Dermoscopy of a skin lesion:
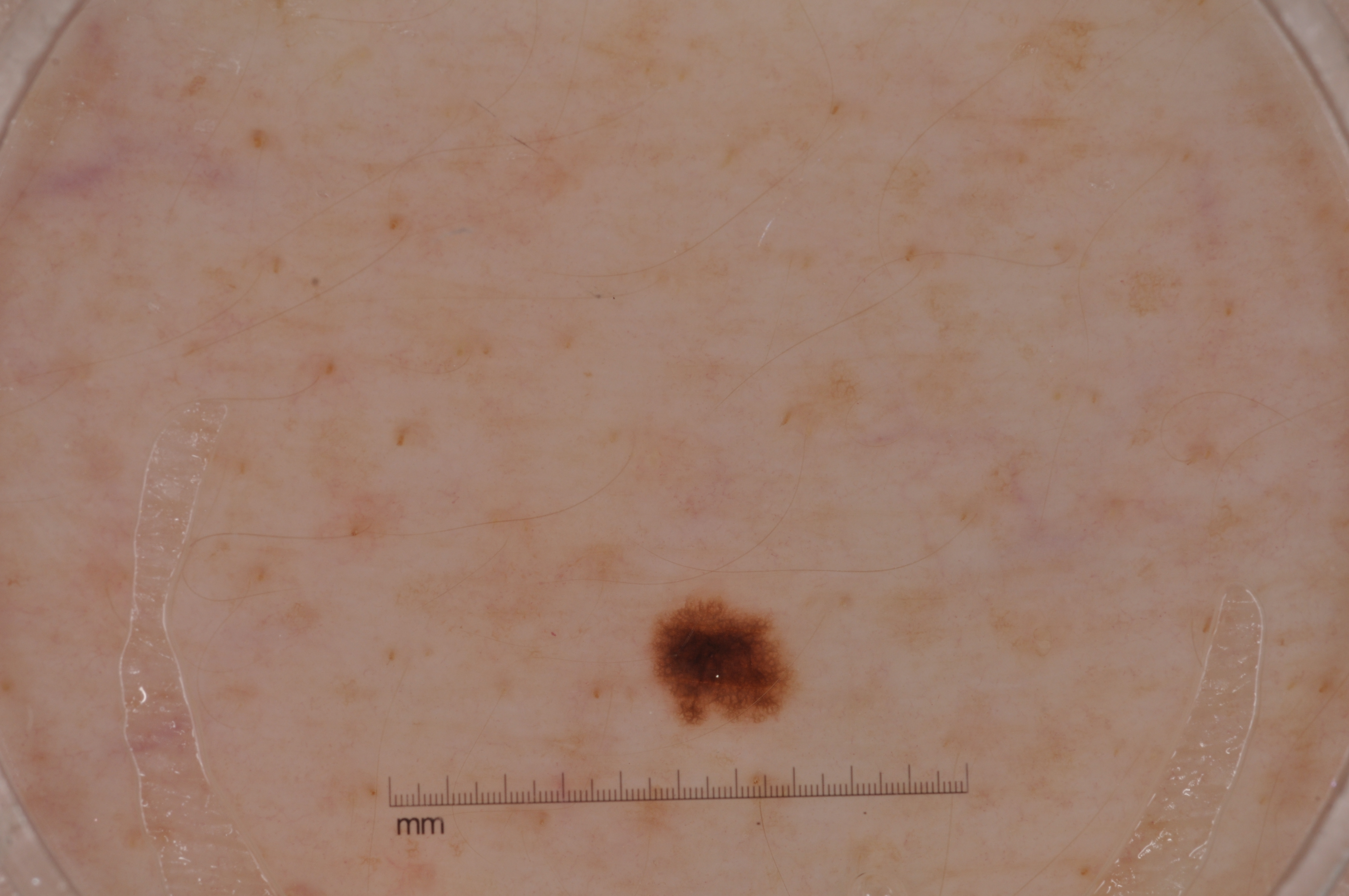location = [639,586,803,732], assessment = a melanocytic nevus.